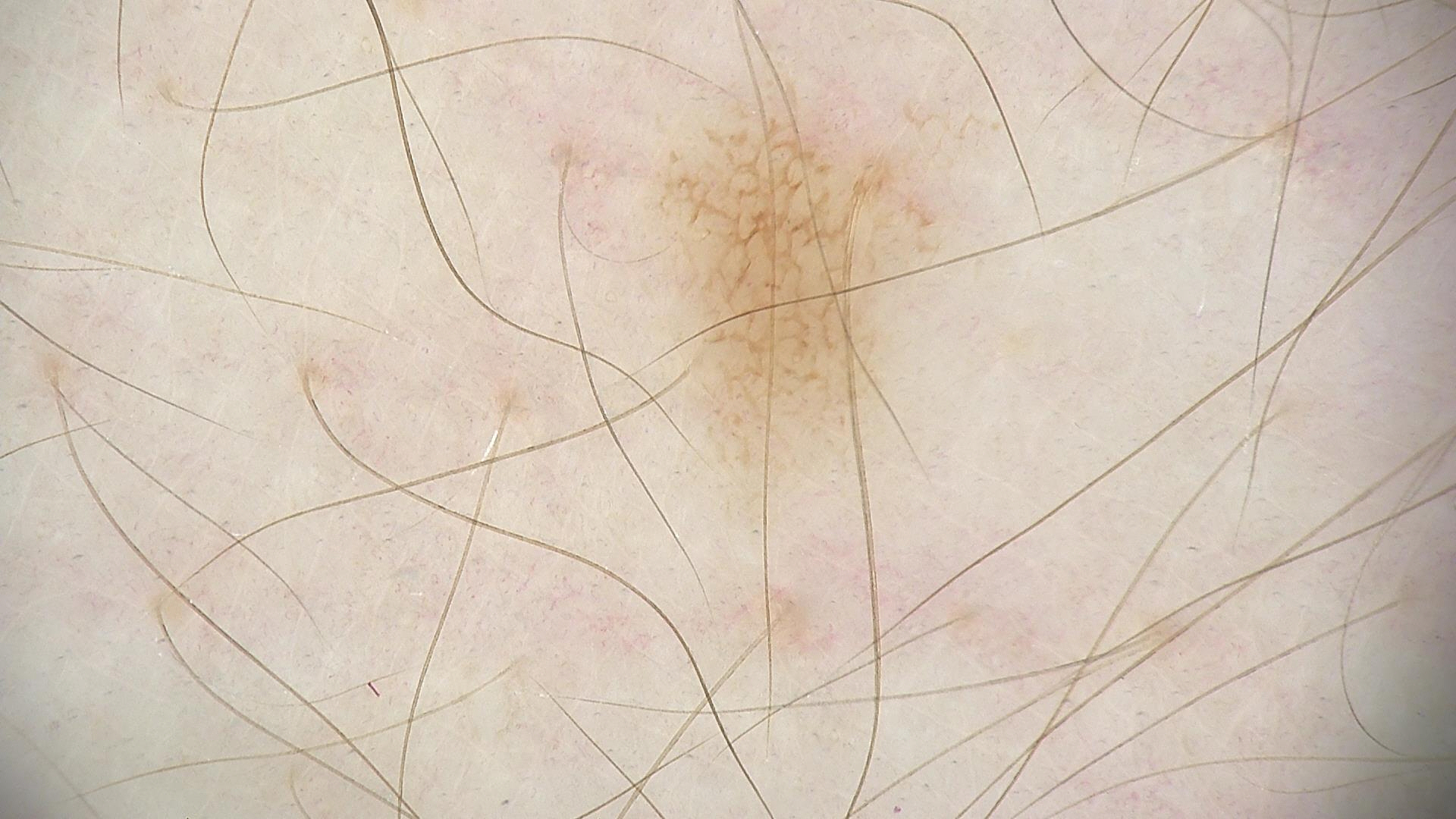image = dermatoscopy; diagnostic label = dysplastic junctional nevus (expert consensus).